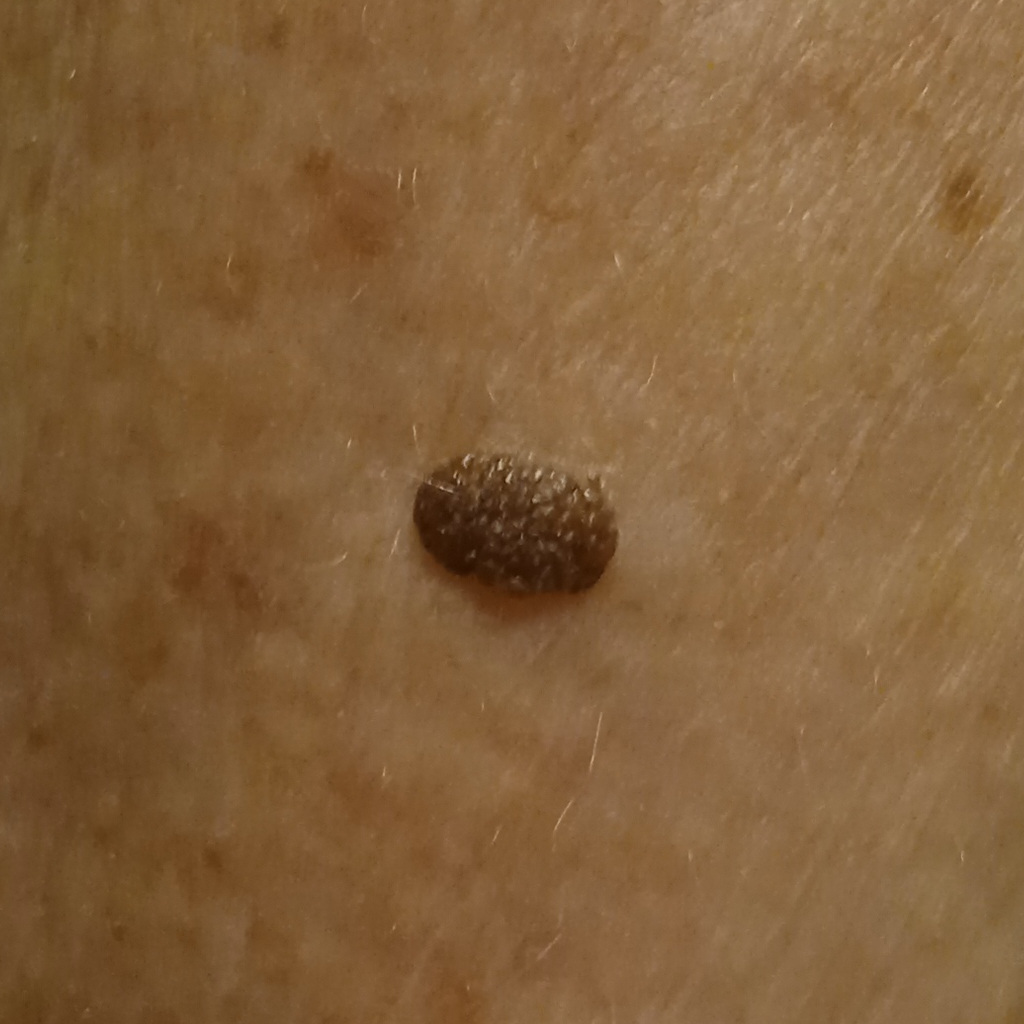A clinical photograph showing a skin lesion.
Imaged for a research study, with no referral diagnosis recorded.
A female subject age 78.
Measuring roughly 5.6 mm.
The lesion was assessed as a seborrheic keratosis.